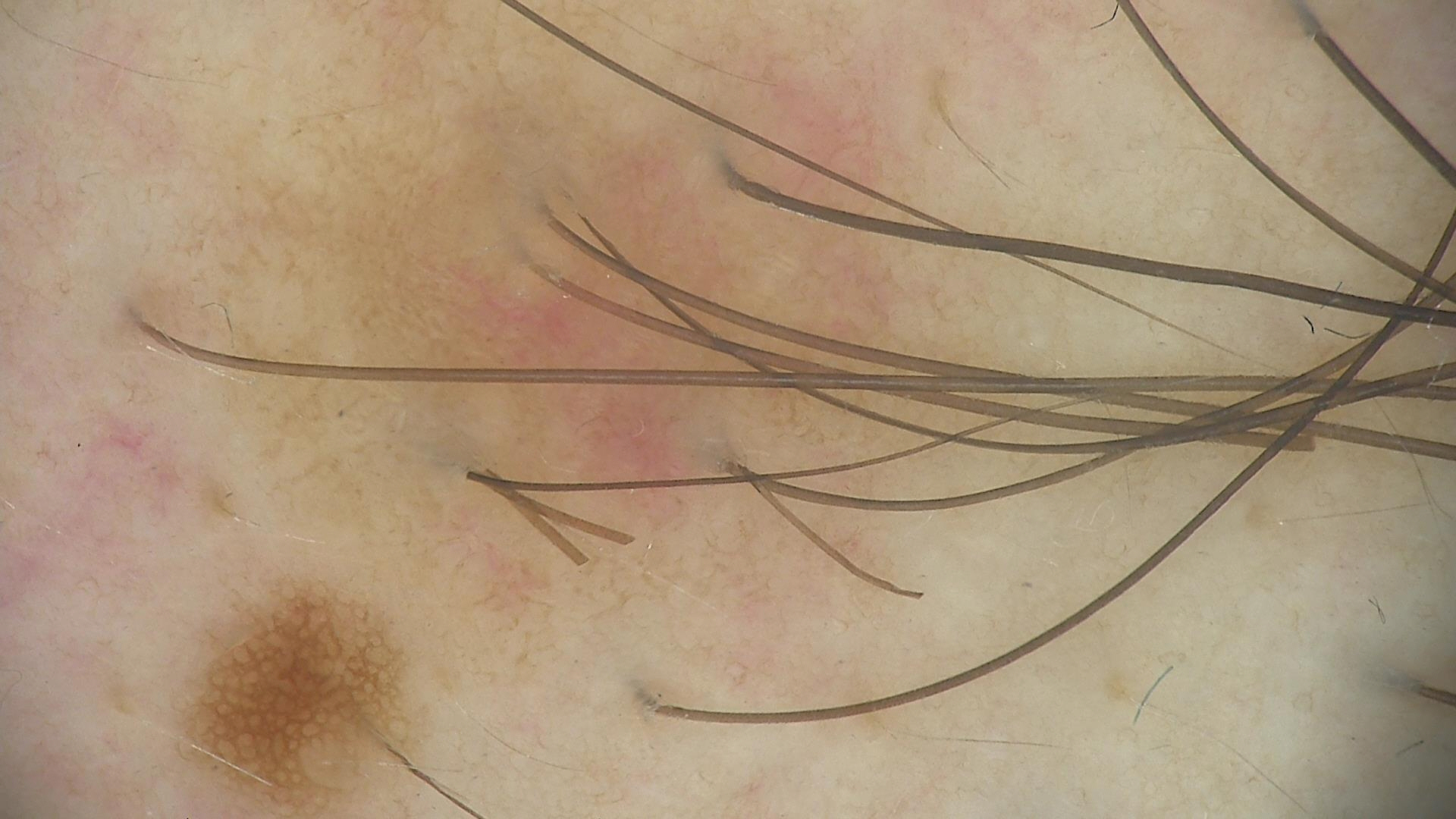The diagnostic label was a dysplastic junctional nevus.